Dermoscopy of a skin lesion.
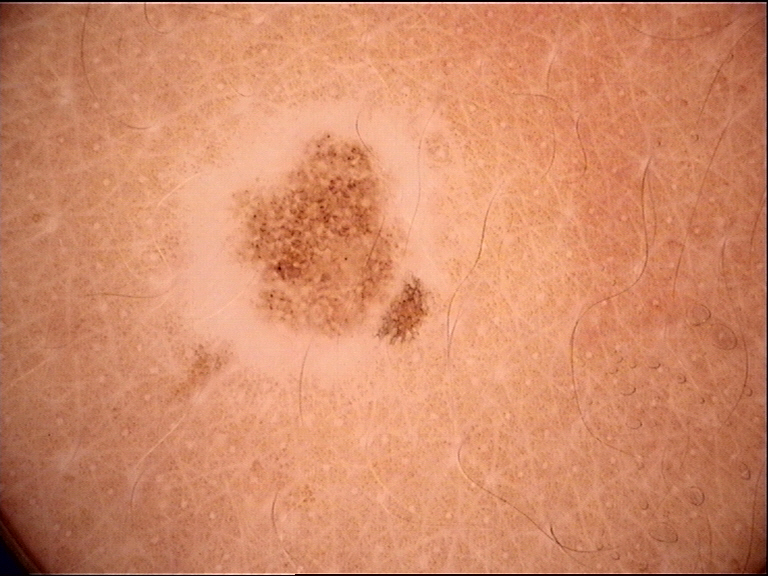The morphology is that of a banal lesion.
Consistent with a junctional nevus.